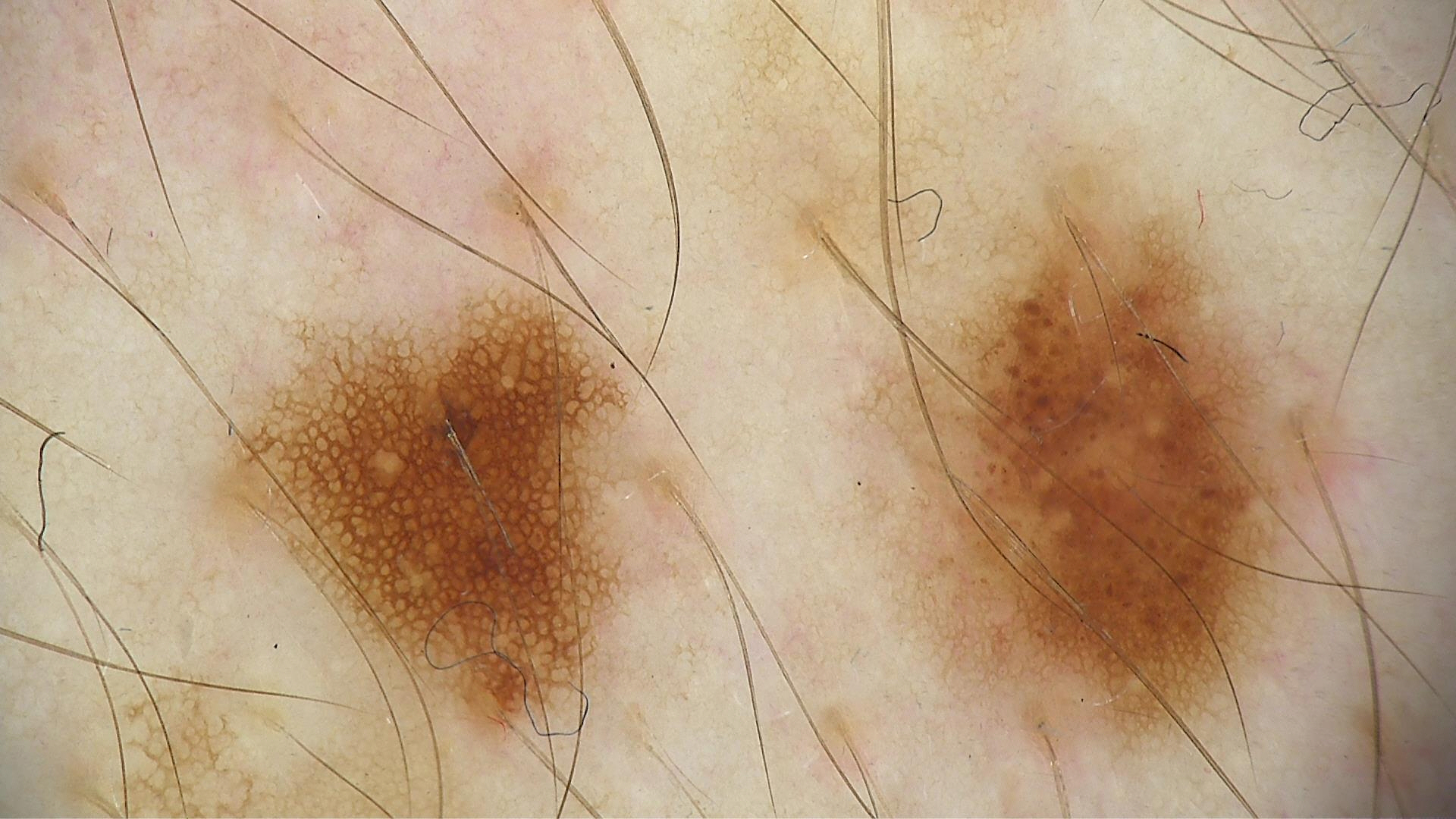<dermoscopy>
<image>dermatoscopy</image>
<diagnosis>
<name>dysplastic junctional nevus</name>
<code>jd</code>
<malignancy>benign</malignancy>
<super_class>melanocytic</super_class>
<confirmation>expert consensus</confirmation>
</diagnosis>
</dermoscopy>